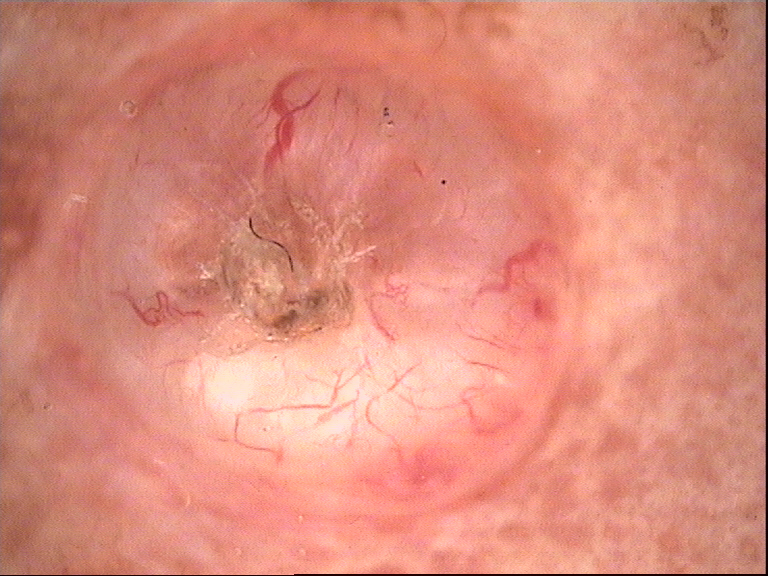{
  "diagnosis": {
    "name": "basal cell carcinoma",
    "code": "bcc",
    "malignancy": "malignant",
    "super_class": "non-melanocytic",
    "confirmation": "histopathology"
  }
}